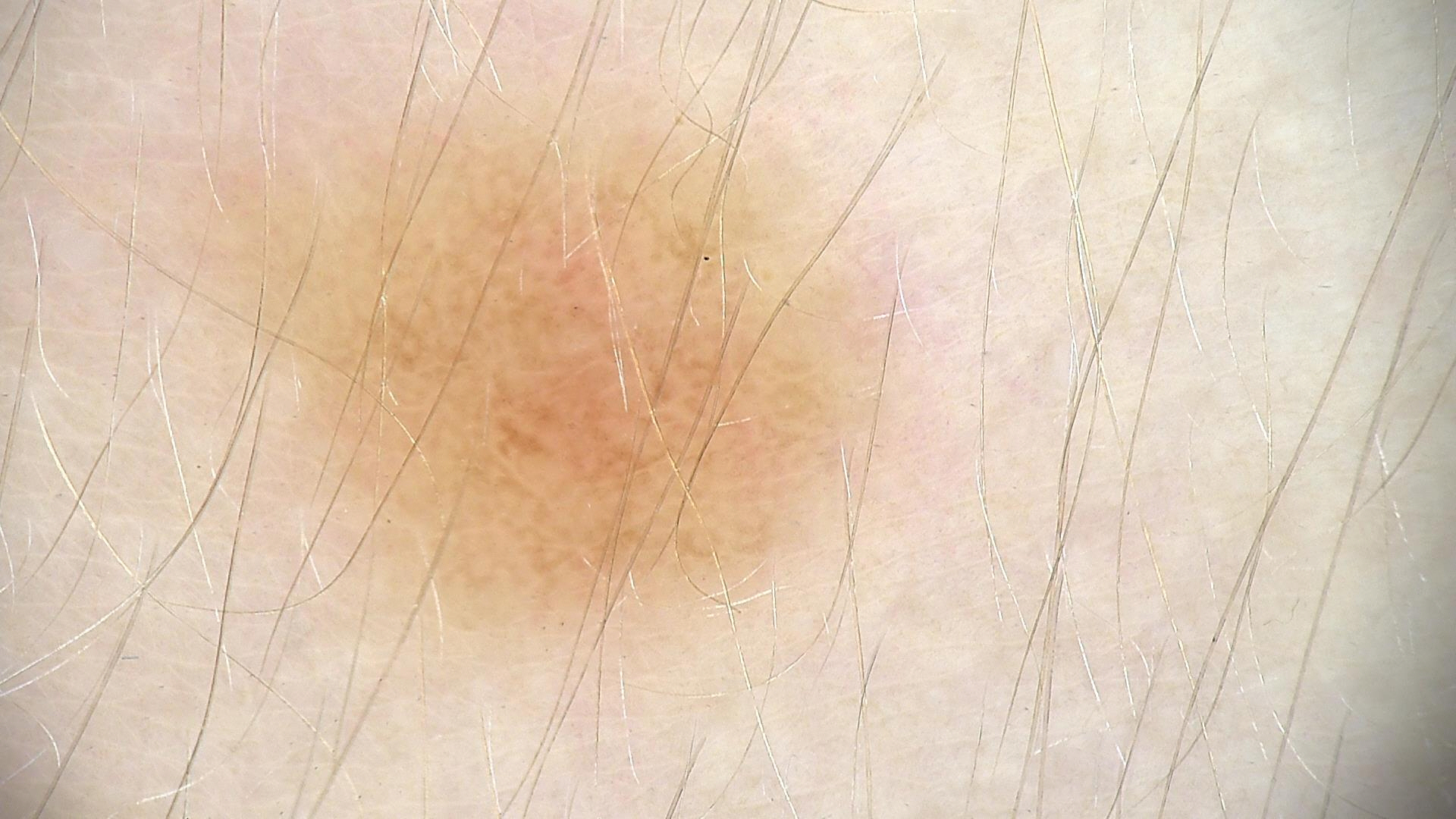class — dysplastic junctional nevus (expert consensus).